An image taken at an angle · male subject, age 40–49 · the arm and leg are involved — 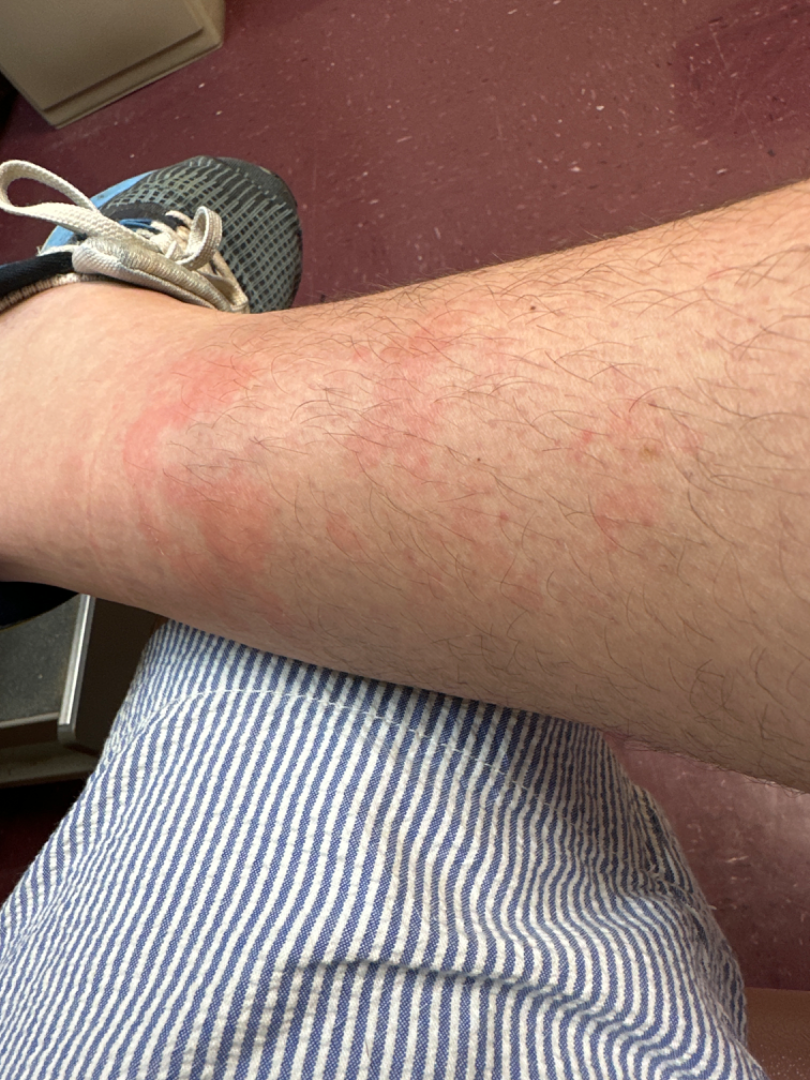{
  "assessment": "could not be assessed"
}